Collected as part of a research study, without a referral diagnosis · the patient reports no immunosuppression and no personal history of skin cancer · the patient describes having a moderate number of moles — 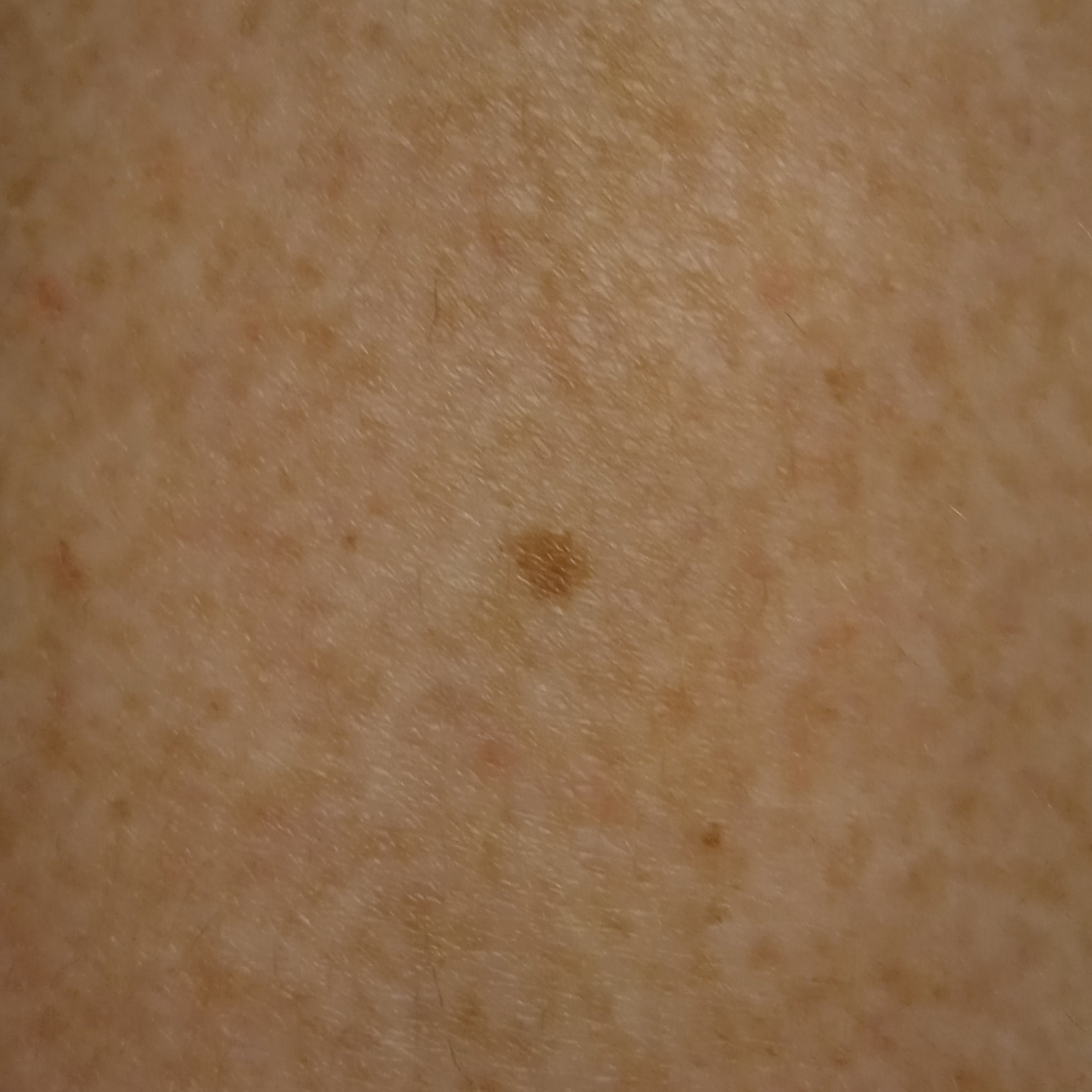Summary:
The lesion is on a leg. Measuring roughly 4.1 mm.
Impression:
The dermatologists' assessment was a melanocytic nevus.